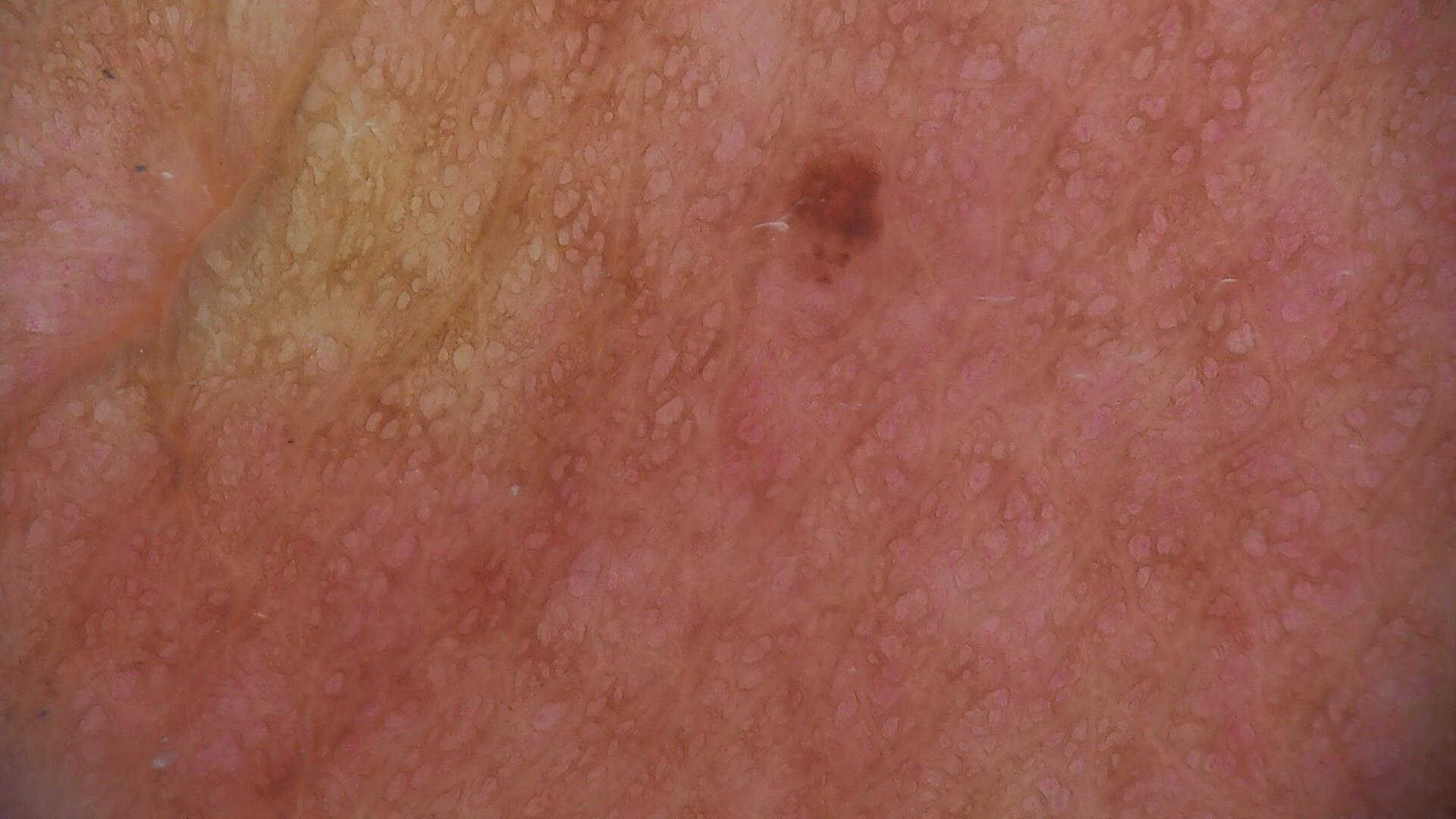A dermoscopy image of a single skin lesion. The morphology is that of a keratinocytic lesion. Classified as a seborrheic keratosis.